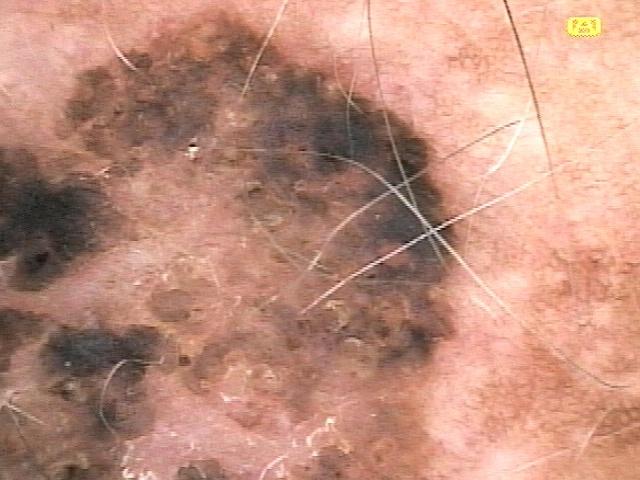Findings:
A skin lesion imaged with a dermatoscope. A male subject aged around 85 or older. The lesion is on the trunk.
Conclusion:
The clinical assessment was a benign lesion — a seborrheic keratosis.